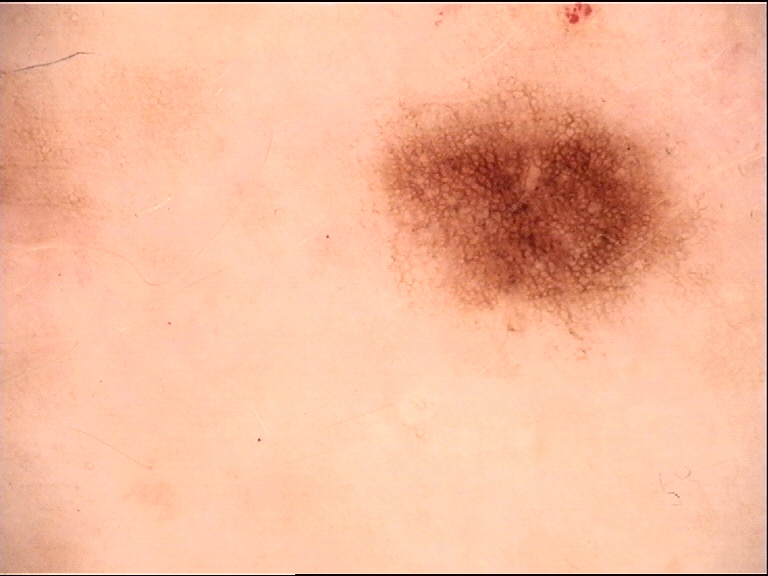label=dysplastic junctional nevus (expert consensus).